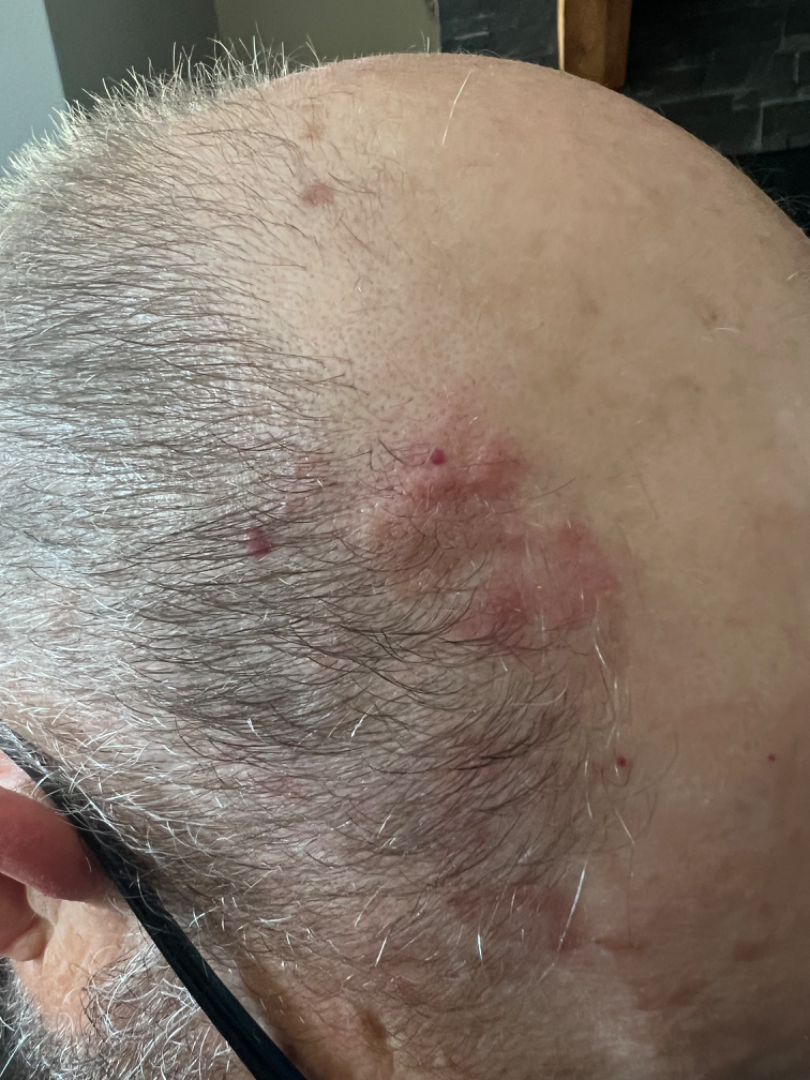affected area = head or neck | patient = male, age 60–69 | constitutional symptoms = none reported | shot type = at an angle | patient describes the issue as = a rash | symptoms = pain | texture = raised or bumpy | symptom duration = less than one week.